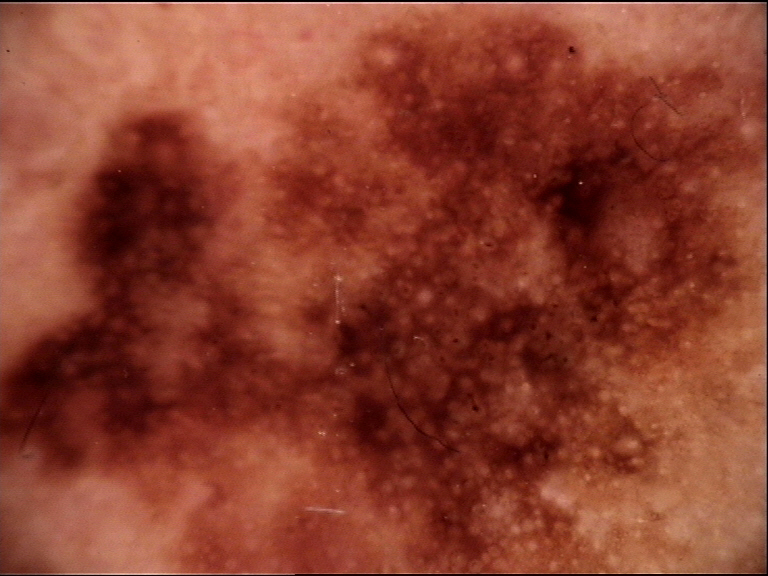{"diagnosis": {"name": "lentigo maligna", "code": "lm", "malignancy": "malignant", "super_class": "melanocytic", "confirmation": "histopathology"}}